The photograph was taken at an angle — 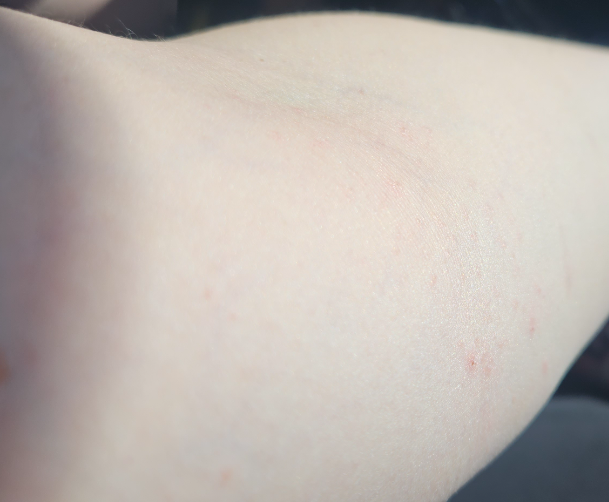Impression: Diagnostic features were not clearly distinguishable in this photograph.